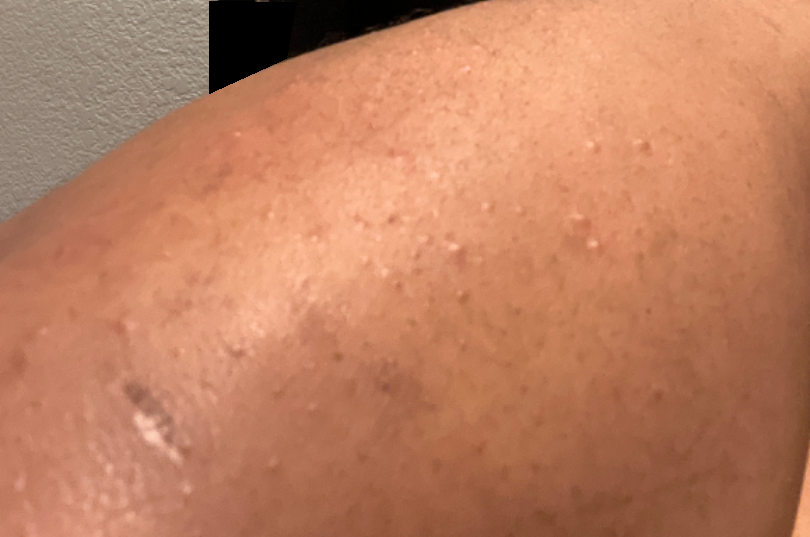assessment = could not be assessed.